A close-up photograph · the subject is 18–29, female · the affected area is the back of the torso, arm, front of the torso and head or neck:
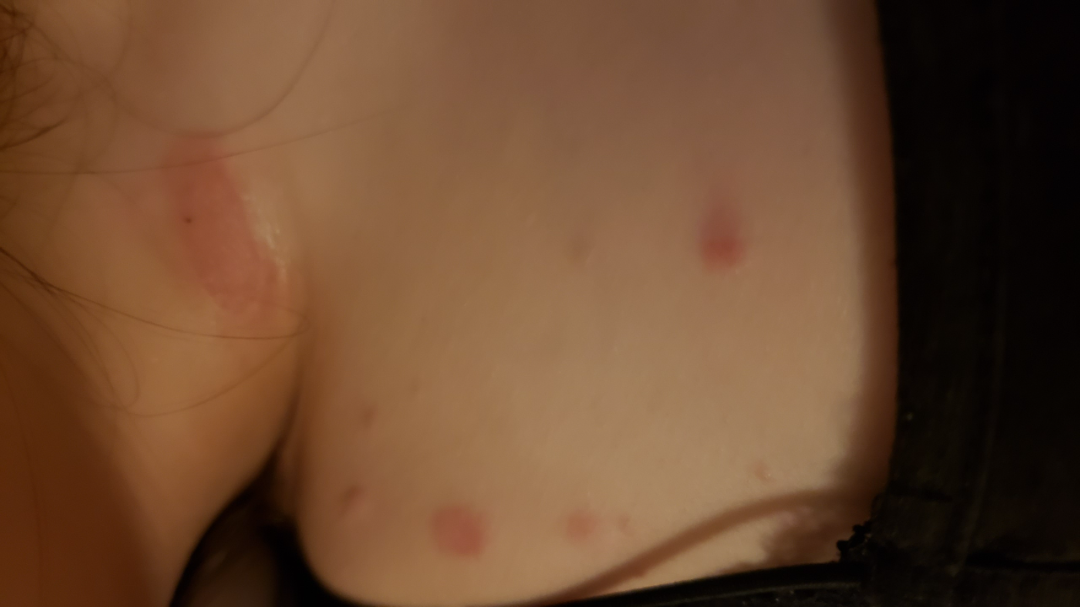| field | value |
|---|---|
| assessment | indeterminate from the photograph |